Located on the head or neck · the patient notes enlargement and itching · the patient notes the condition has been present for less than one week · self-categorized by the patient as a rash · the photograph is a close-up of the affected area · the lesion is described as raised or bumpy: 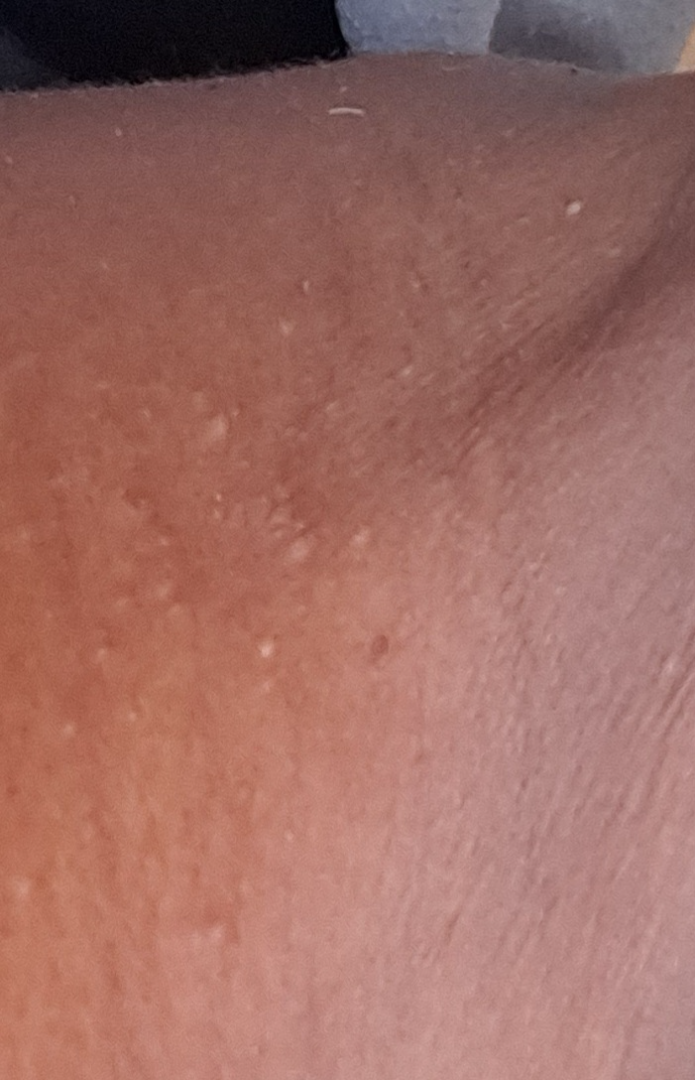Q: Could the case be diagnosed?
A: indeterminate from the photograph